Referred for assessment of suspected melanoma. A clinical close-up of a skin lesion. A female patient 50 years of age. By self-report, no prior organ transplant and no personal history of cancer. The patient describes having a moderate number of moles:
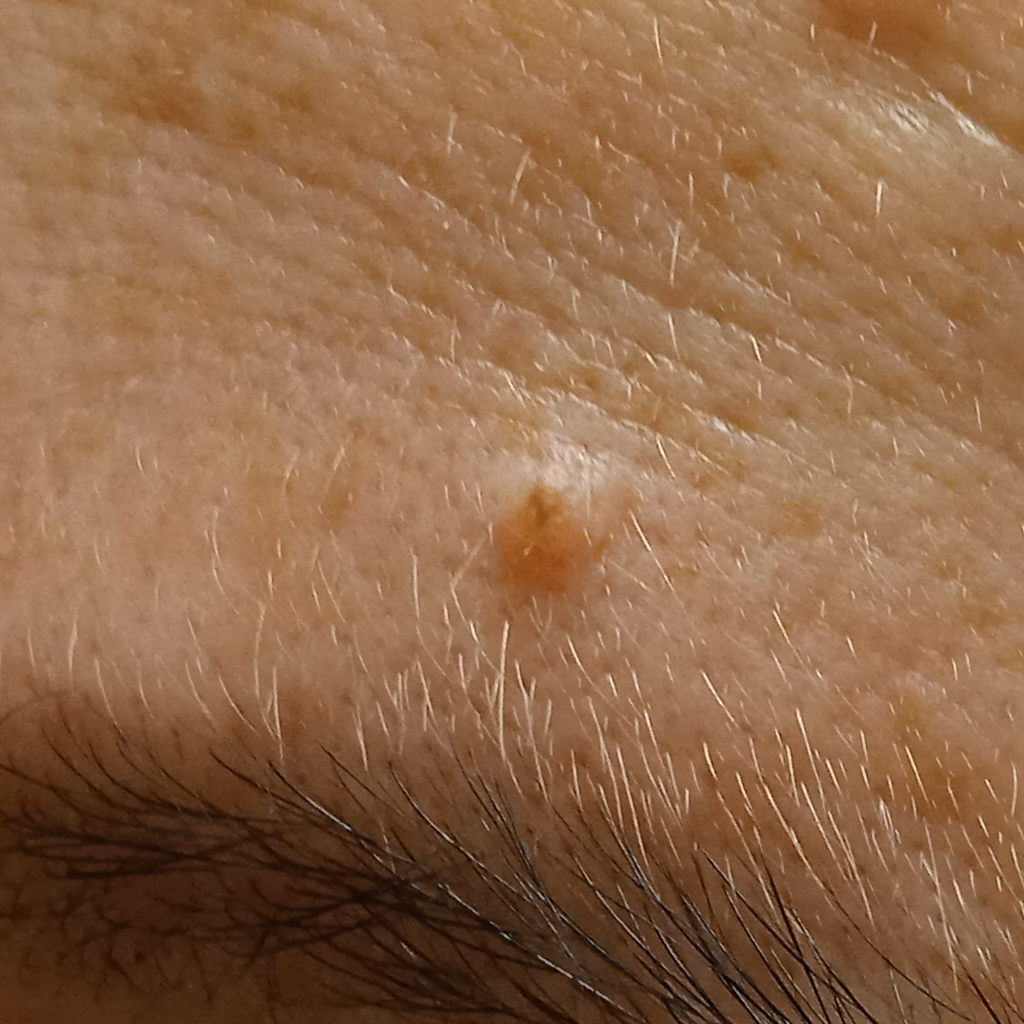| field | value |
|---|---|
| anatomic site | the face |
| size | 1.8 mm |
| diagnosis | melanocytic nevus (dermatologist consensus) |